A macroscopic clinical photograph of a skin lesion; a male patient aged 83; acquired for a research image collection, with no referral diagnosis — 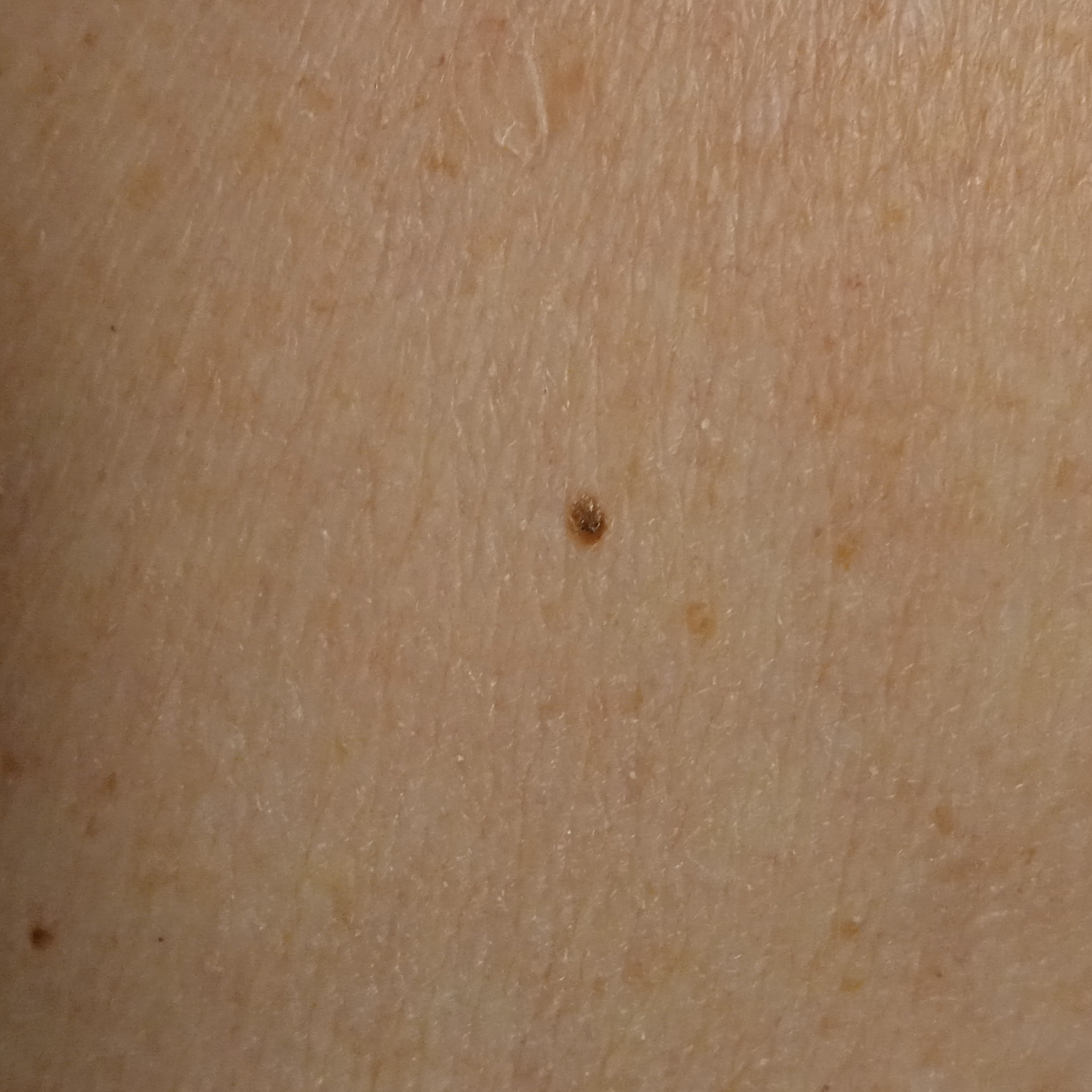Q: Where is the lesion?
A: the back
Q: How large is the lesion?
A: 2.5 mm
Q: What was the diagnosis?
A: seborrheic keratosis (dermatologist consensus)